The photograph is a close-up of the affected area, located on the arm.
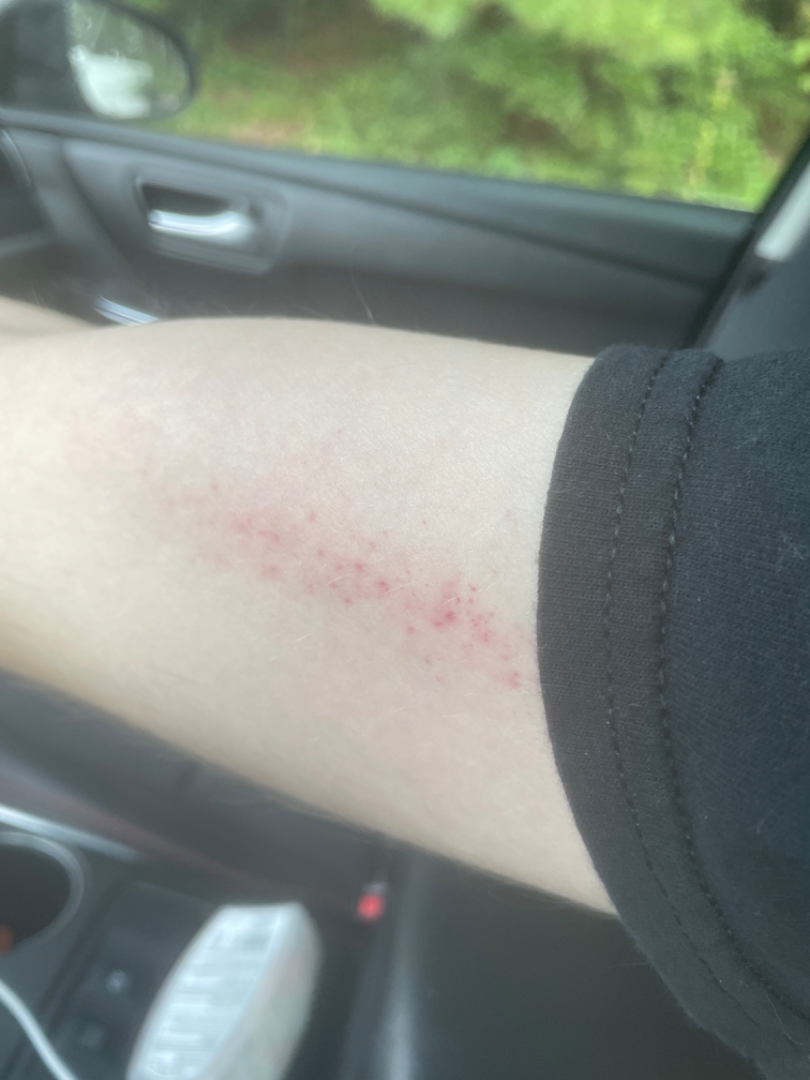Impression:
On dermatologist assessment of the image, Abrasion, scrape, or scab and petechiae were each considered, in no particular order; lower on the differential is Eczema.